Located on the top or side of the foot and leg; the lesion is described as raised or bumpy; this image was taken at an angle; reported lesion symptoms include itching: 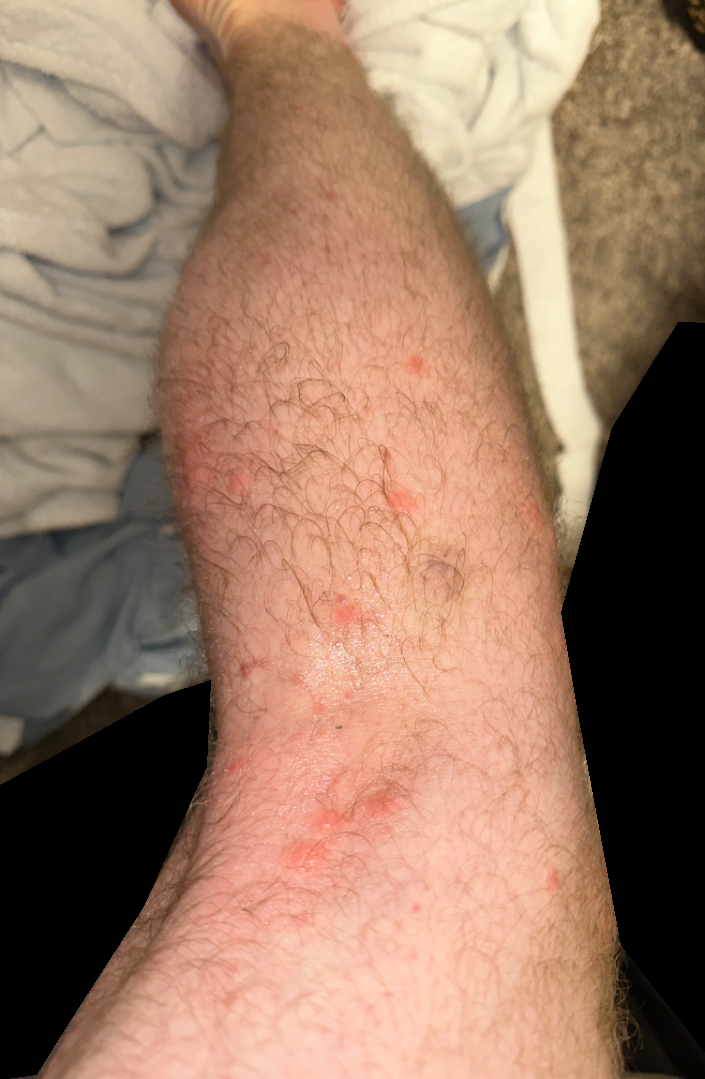<summary>
  <assessment>unable to determine</assessment>
</summary>